The lesion involves the front of the torso and back of the torso · present for more than one year · this is a close-up image: 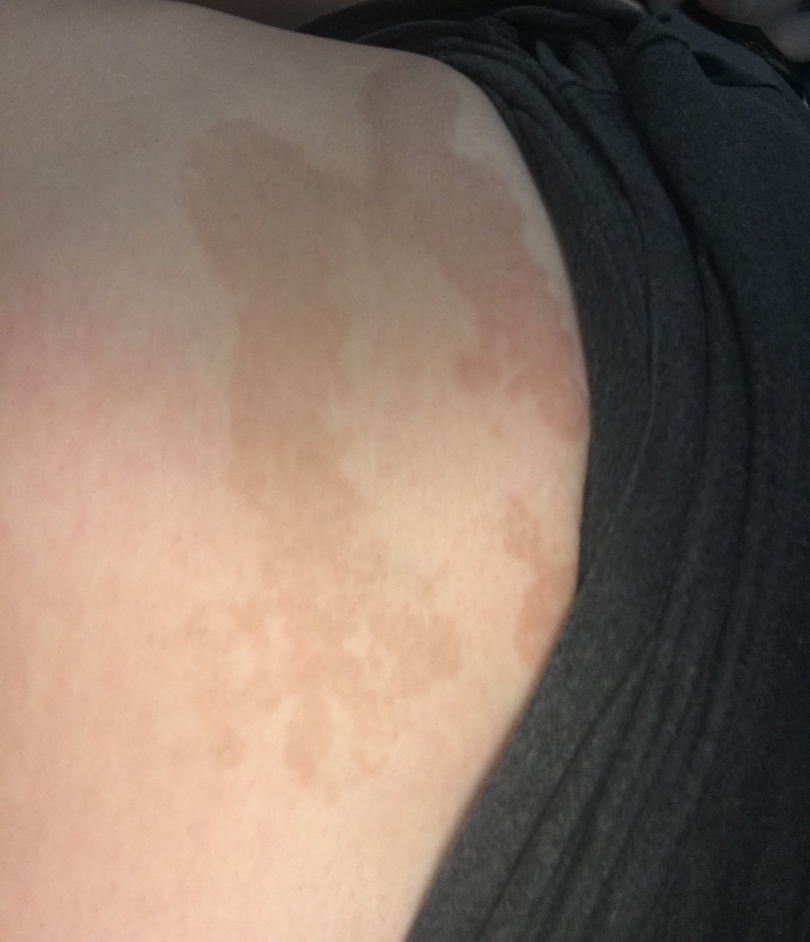The condition could not be reliably identified from the image.